A close-up photograph; the leg is involved; female patient, age 50–59.
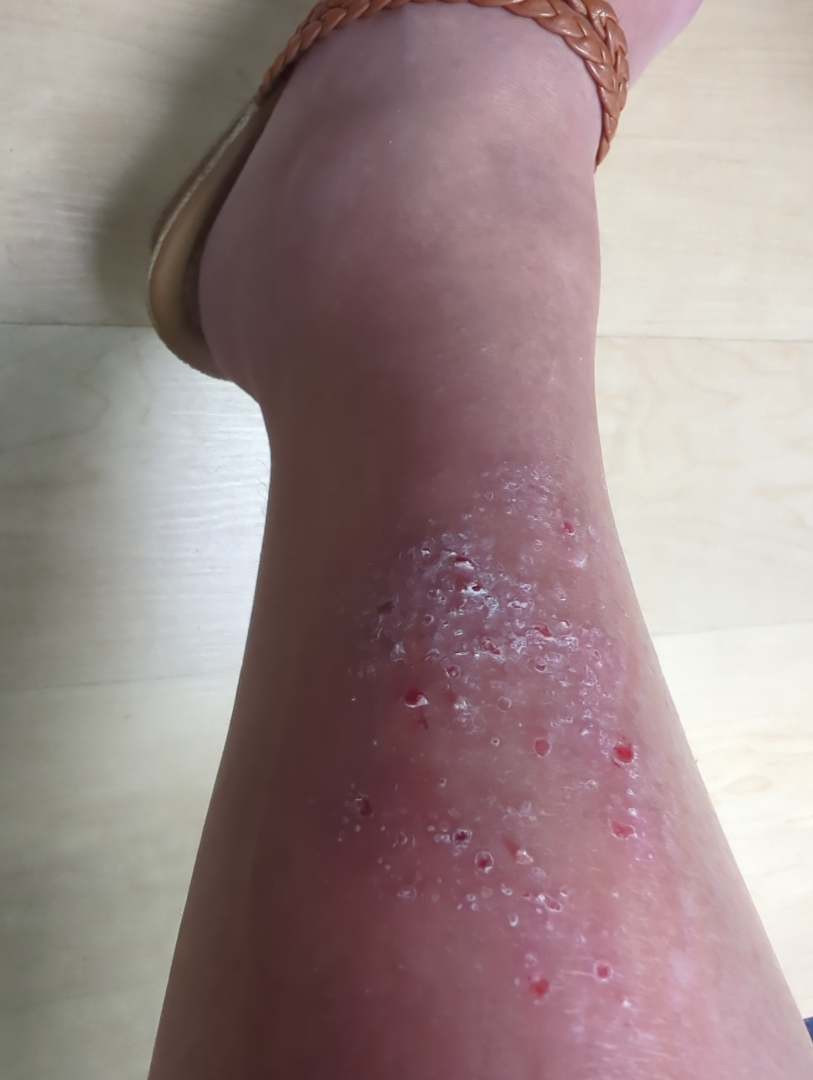Impression: The reviewing dermatologist's impression was: Tinea (0.33); Psoriasis (0.33); Lichen Simplex Chronicus (0.33).